A contact-polarized dermoscopy image of a skin lesion · recorded as FST II · a female subject aged 23-27: 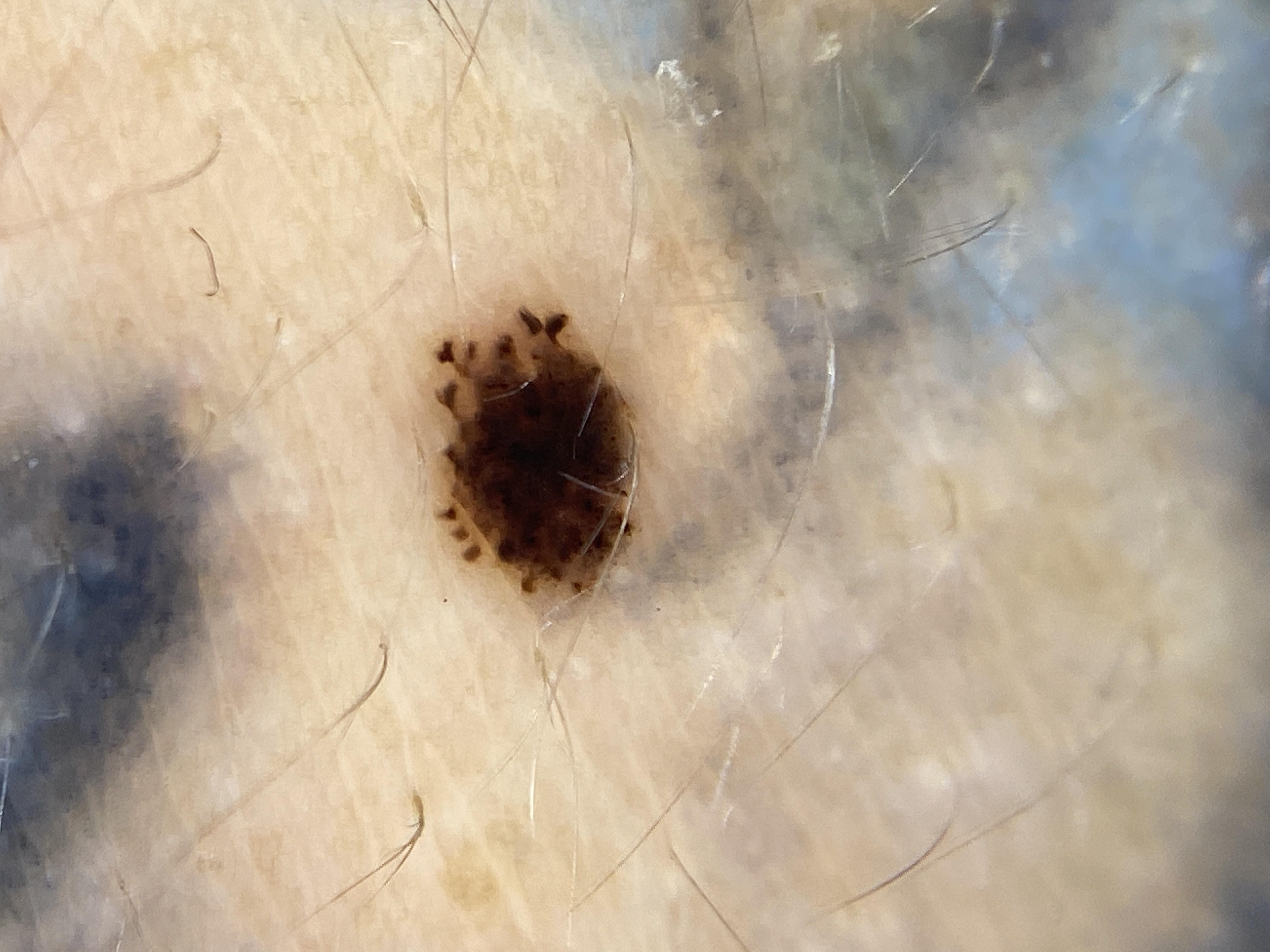The lesion is located on the trunk (the posterior trunk). Confirmed on histopathology as a lesion of melanocytic origin — a nevus.